This image was taken at an angle. The affected area is the head or neck.
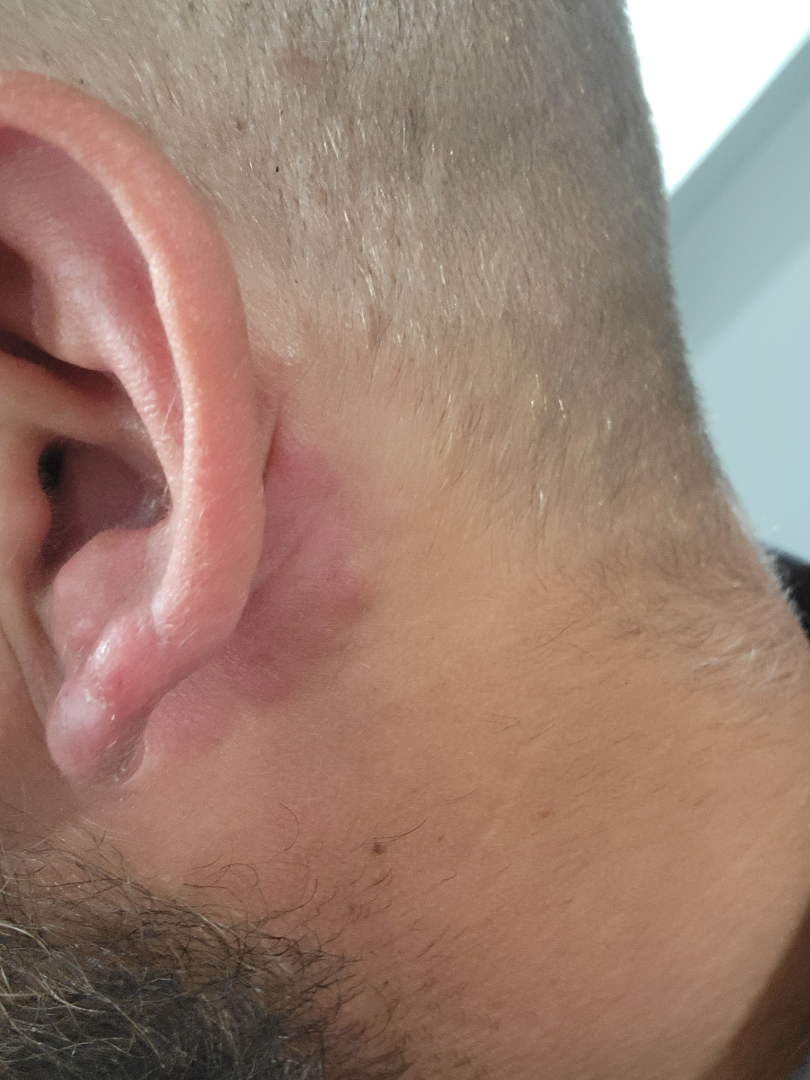Case summary:
– diagnostic considerations · a single dermatologist reviewed the case: Allergic Contact Dermatitis and Granulomatous disorder of the skin and subcutaneous tissue were each considered, in no particular order